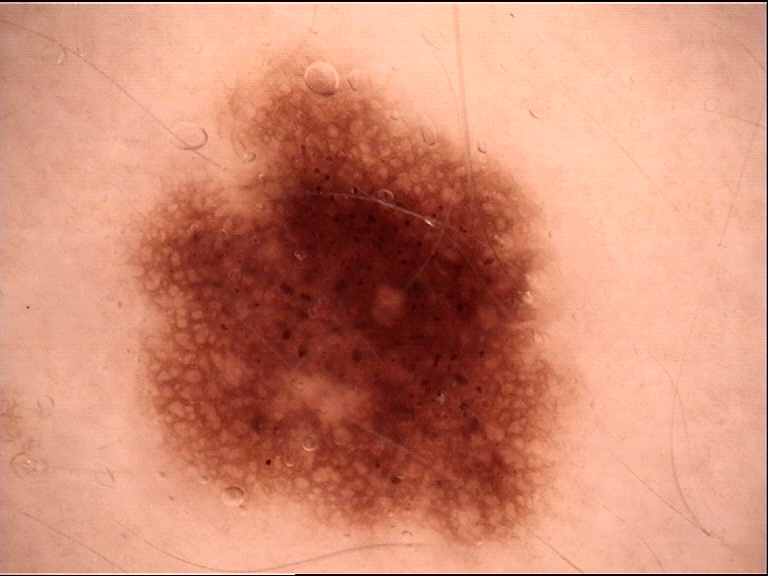A dermoscopy image of a single skin lesion.
The diagnostic label was a dysplastic junctional nevus.